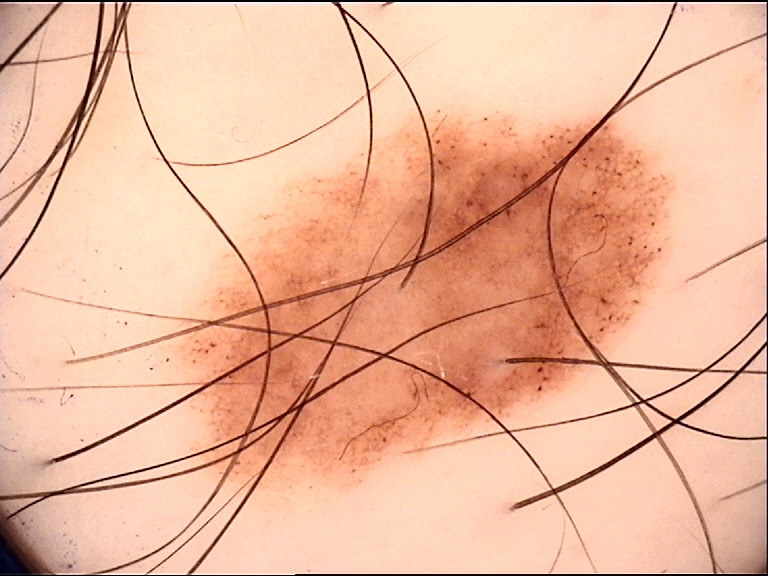| feature | finding |
|---|---|
| diagnosis | dysplastic junctional nevus (expert consensus) |